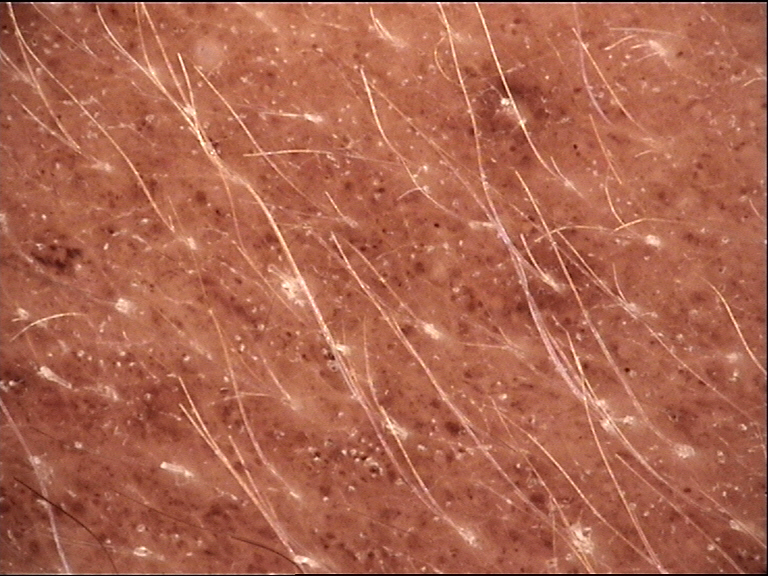  diagnosis:
    name: congenital compound nevus
    code: ccb
    malignancy: benign
    super_class: melanocytic
    confirmation: expert consensus